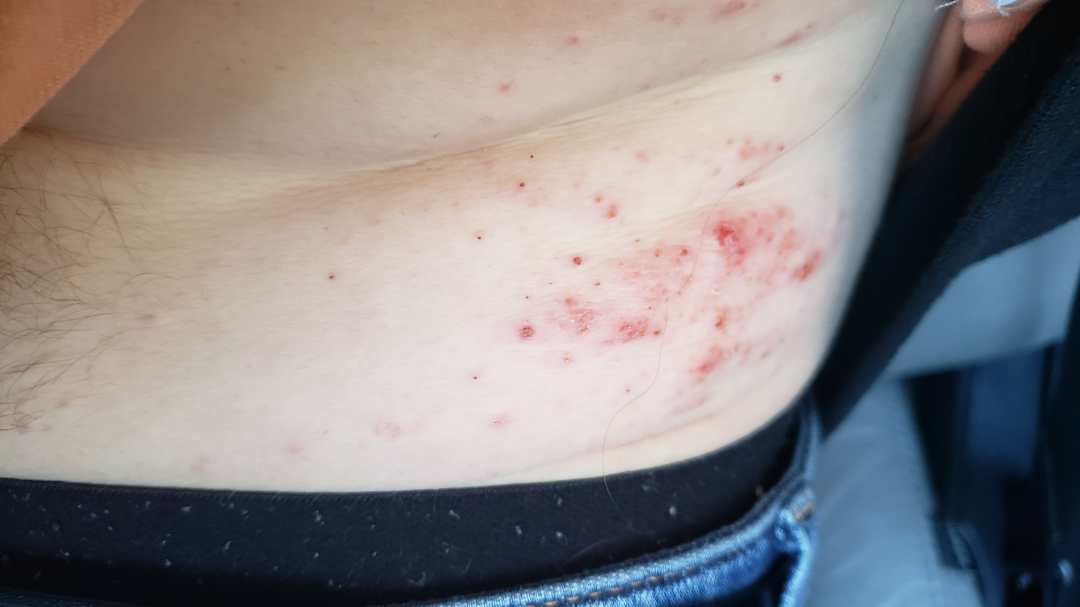The condition could not be reliably identified from the image. No associated systemic symptoms reported. An image taken at a distance. Texture is reported as rough or flaky and raised or bumpy. The patient described the issue as a rash. Symptoms reported: bothersome appearance and itching. The lesion involves the head or neck, leg, top or side of the foot, back of the torso, arm, front of the torso and back of the hand.